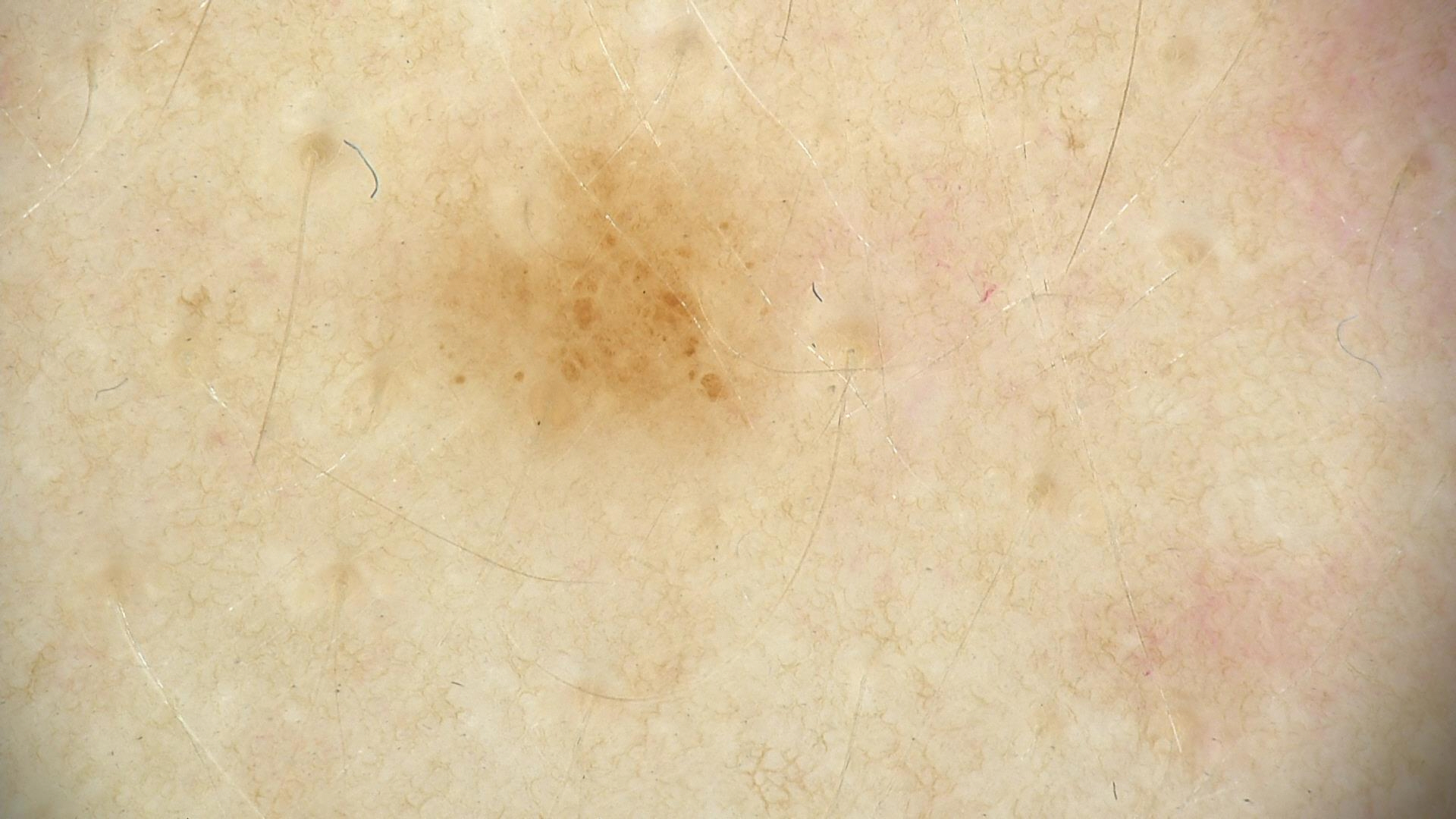A dermatoscopic image of a skin lesion.
Diagnosed as a benign lesion — a dysplastic junctional nevus.